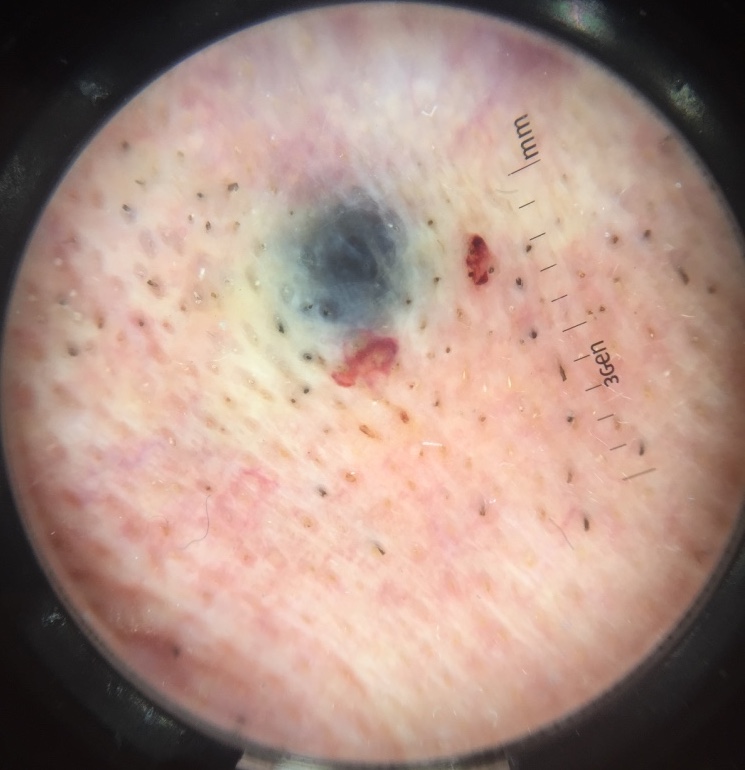imaging — dermatoscopy; classification — dermal, banal; assessment — blue nevus (expert consensus).